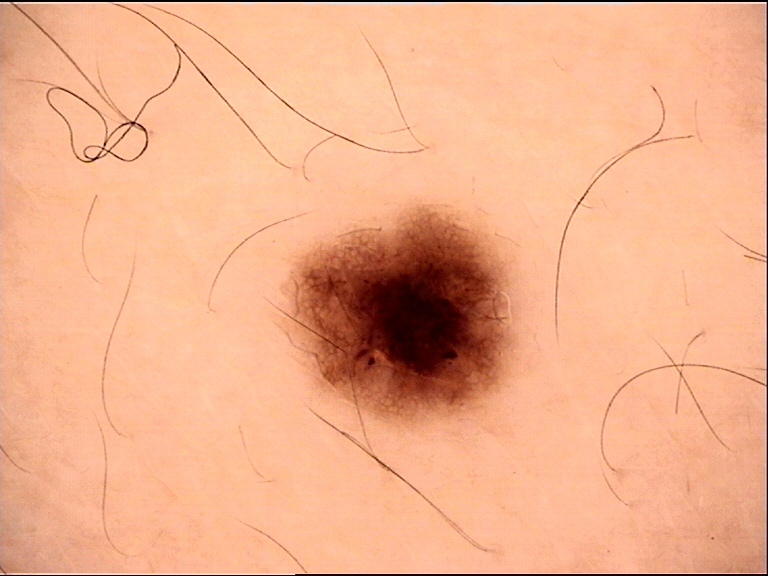assessment: dysplastic junctional nevus (expert consensus)